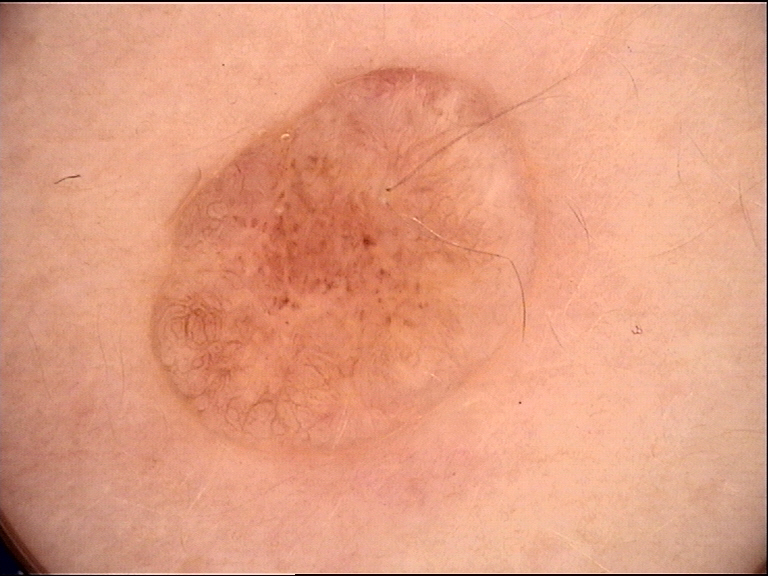imaging: dermatoscopy; diagnostic label: dermal nevus (expert consensus).